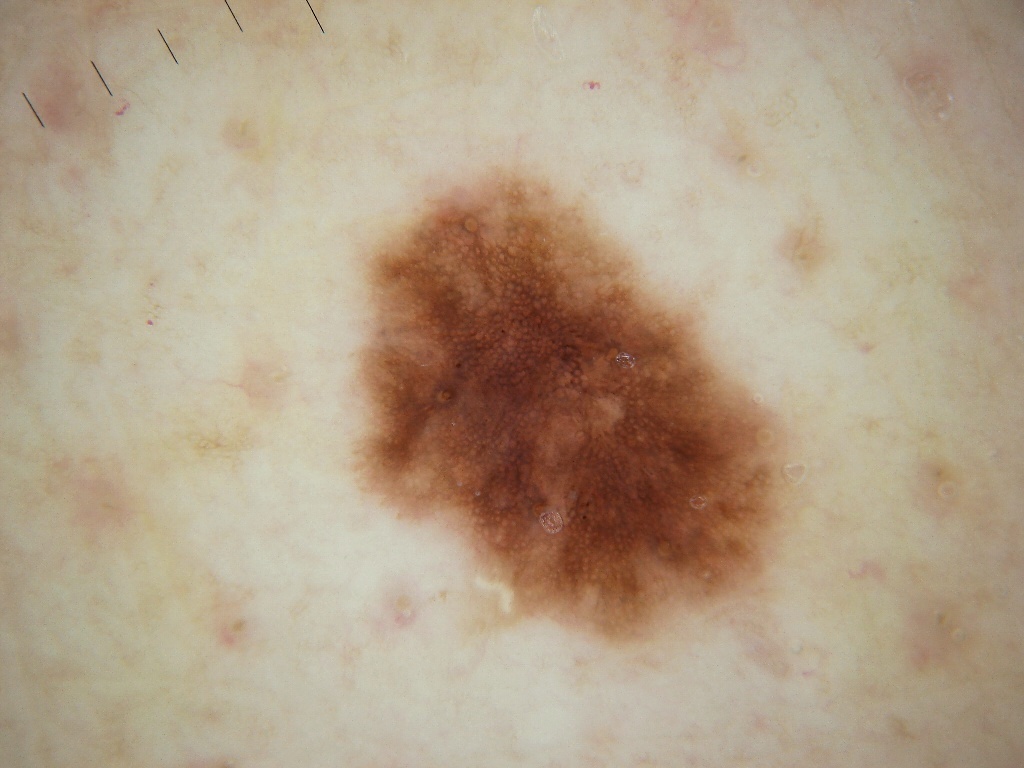modality=dermoscopy
extent=moderate
features=pigment network
lesion location=[357, 172, 795, 644]
diagnostic label=a melanocytic nevus